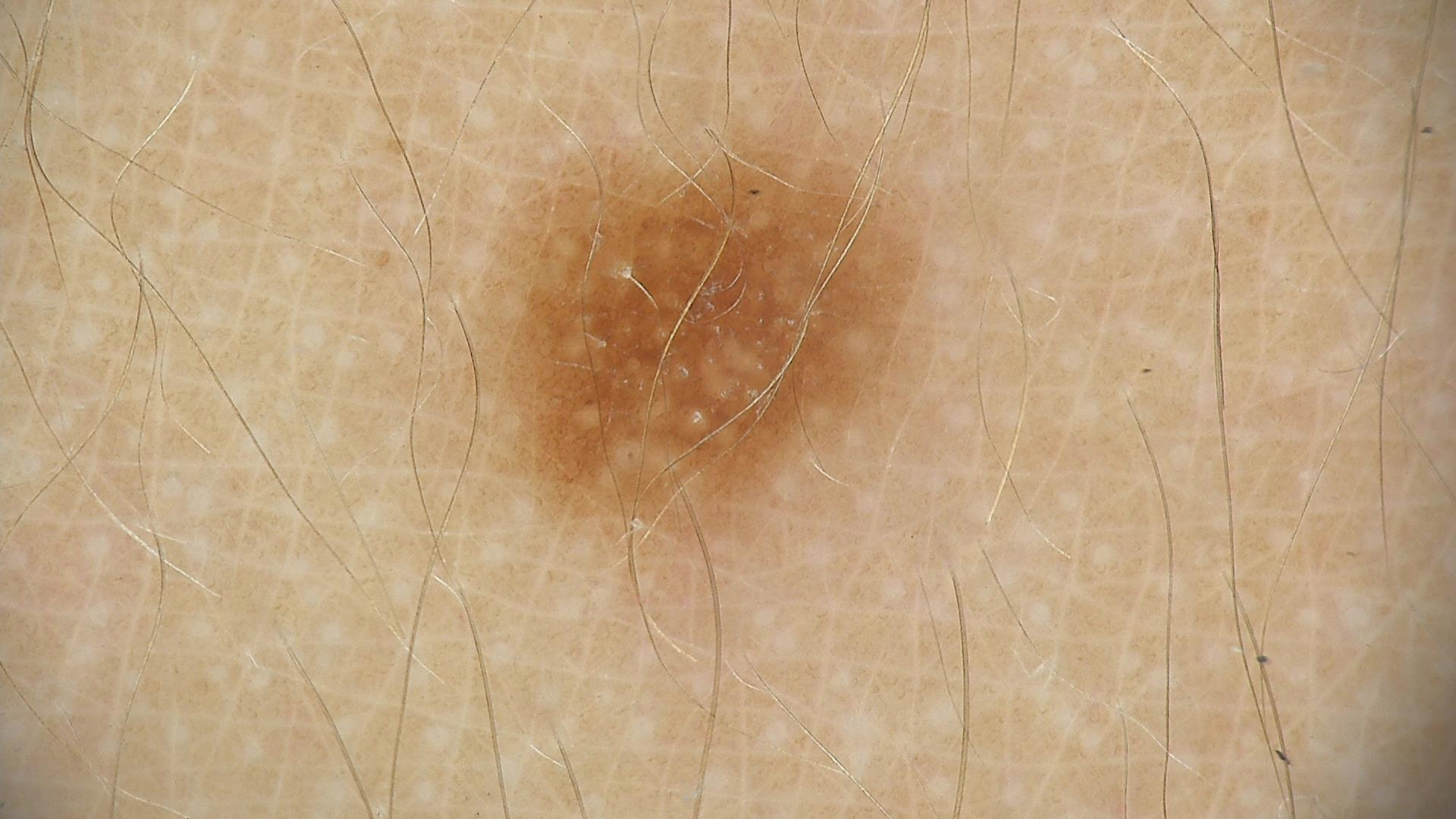Findings:
A dermoscopic photograph of a skin lesion.
Impression:
The diagnostic label was a dysplastic junctional nevus.